Self-categorized by the patient as a rash · an image taken at an angle · the lesion is associated with enlargement, burning, itching and bothersome appearance · present for one to four weeks · the patient is a female aged 40–49 · the lesion involves the arm — 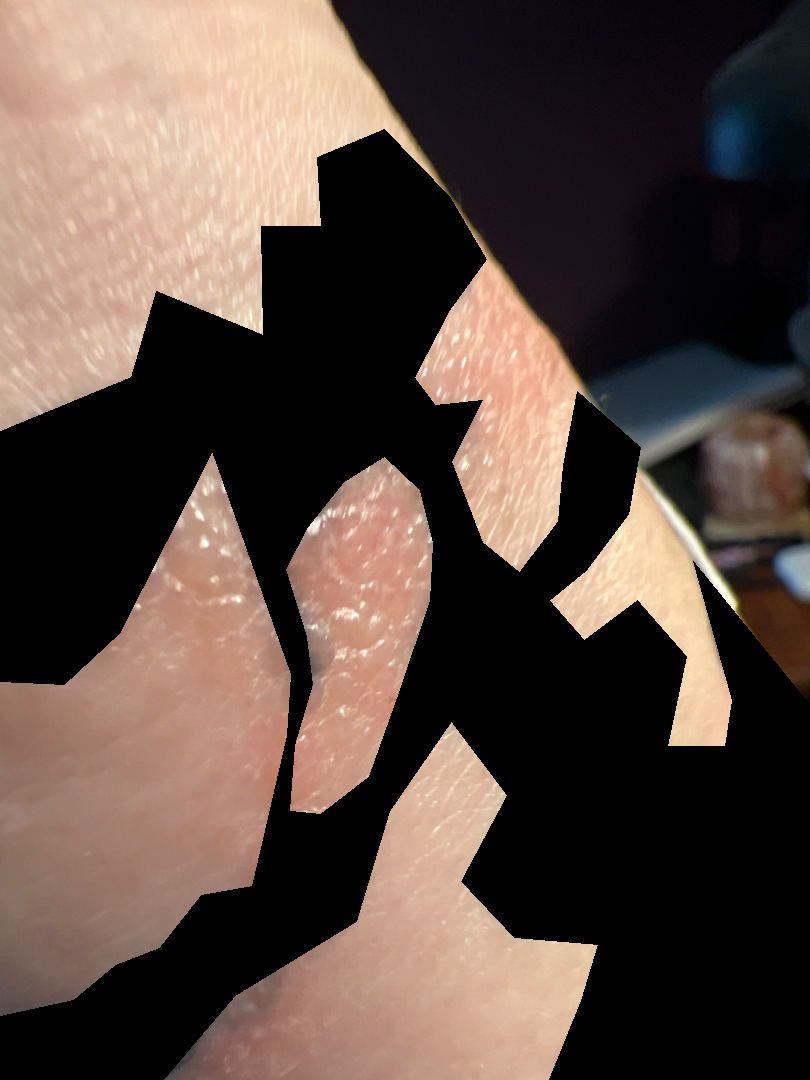{"differential": {"leading": ["Allergic Contact Dermatitis"], "considered": ["Herpes Zoster"], "unlikely": ["Impetigo"]}}